A dermoscopic image of a skin lesion.
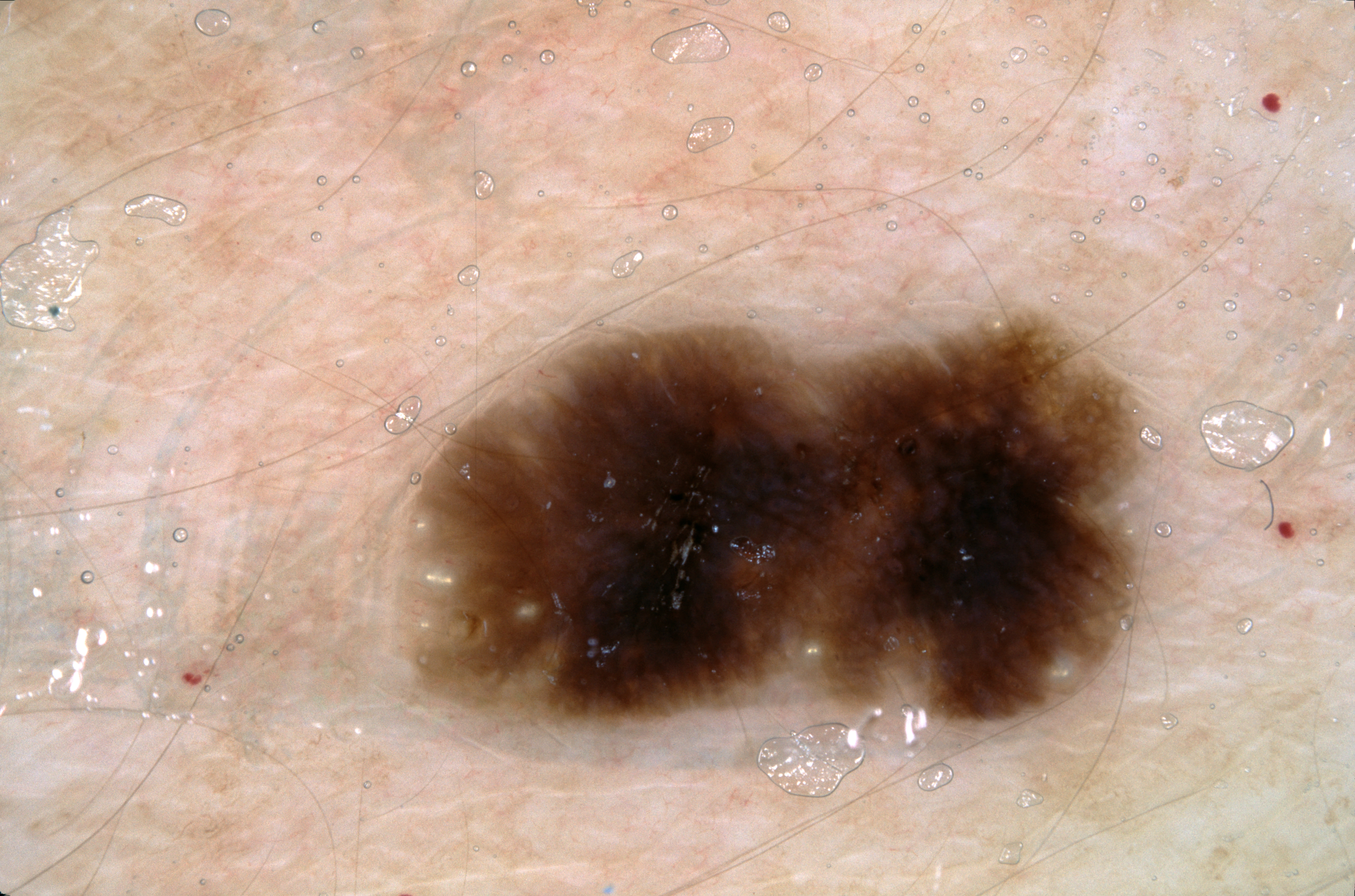<case>
<dermoscopic_features>
  <present>pigment network, milia-like cysts</present>
  <absent>streaks, negative network</absent>
</dermoscopic_features>
<lesion_location>
  <bbox_xyxy>424, 322, 1143, 728</bbox_xyxy>
</lesion_location>
<diagnosis>
  <name>seborrheic keratosis</name>
  <malignancy>benign</malignancy>
  <lineage>keratinocytic</lineage>
  <provenance>clinical</provenance>
</diagnosis>
</case>